A dermoscopic close-up of a skin lesion.
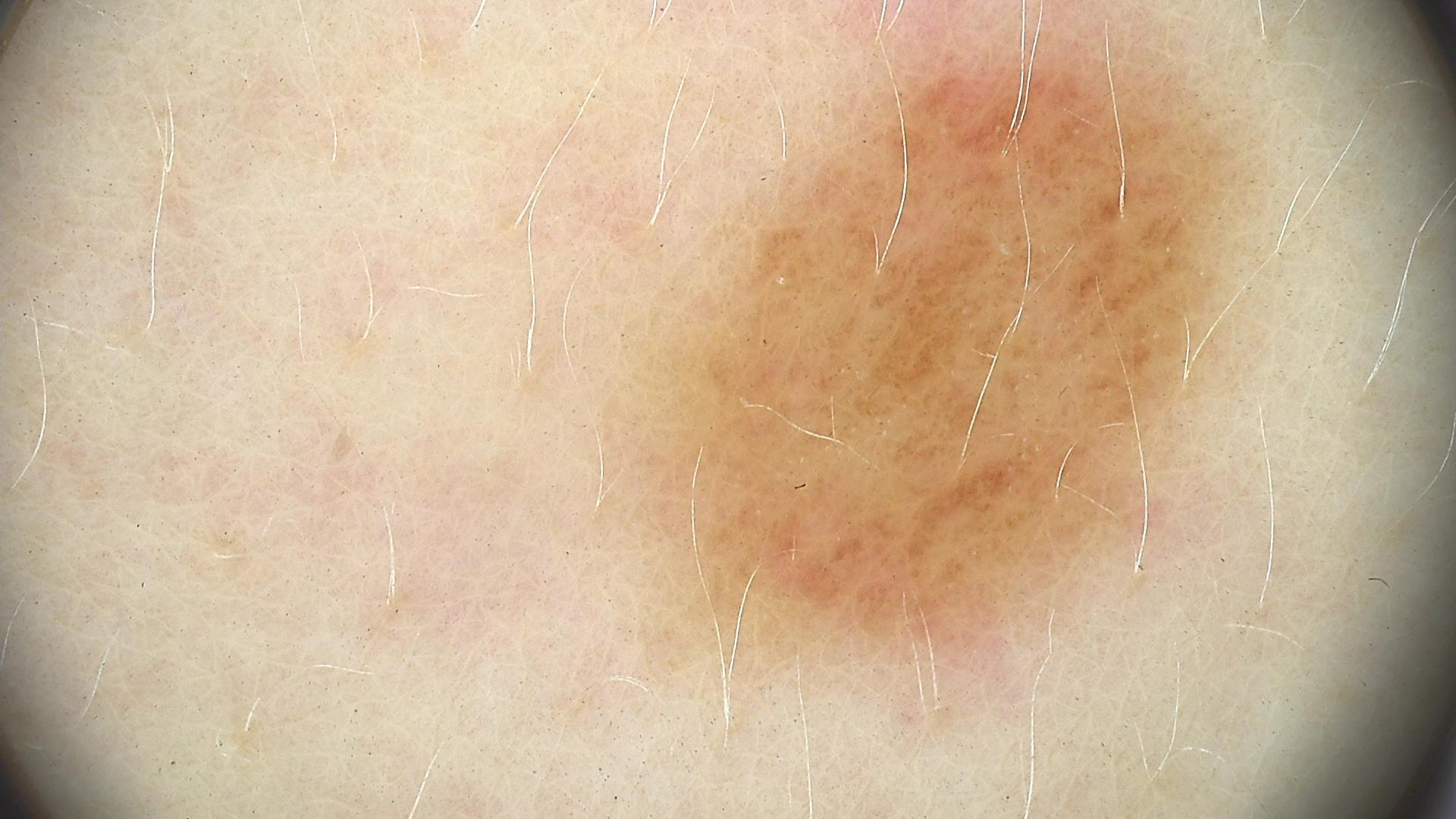class — dysplastic junctional nevus (expert consensus).